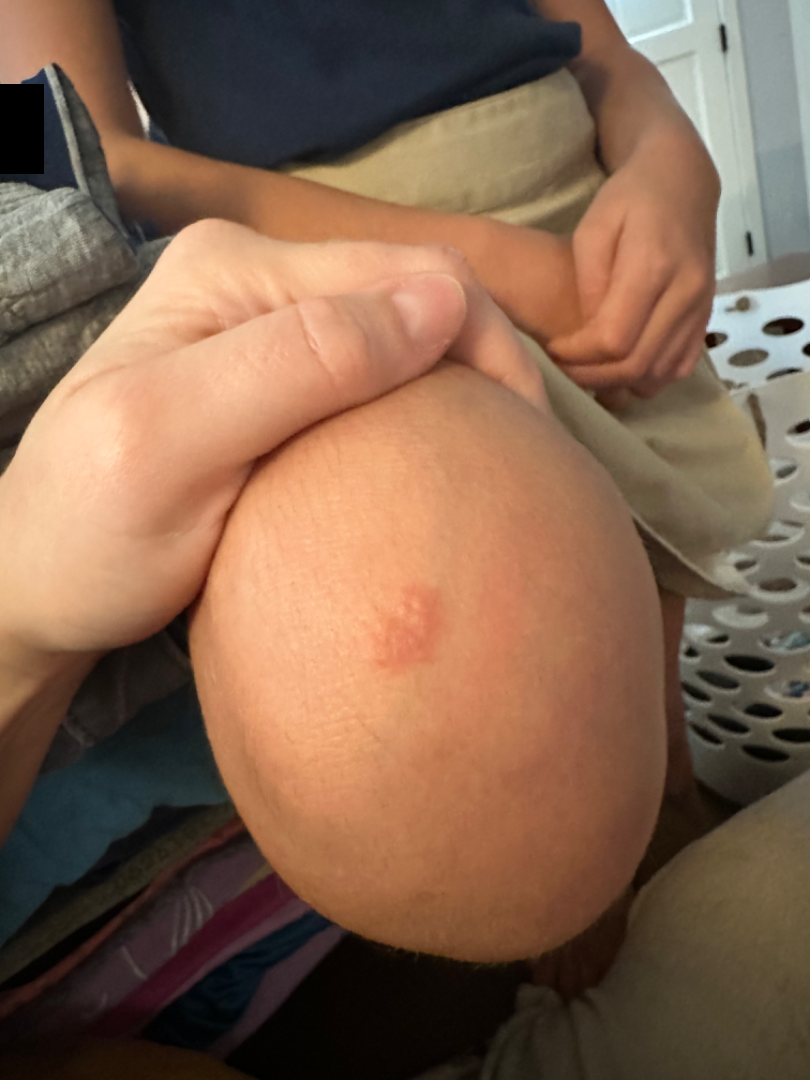Review: The case was indeterminate on photographic review.